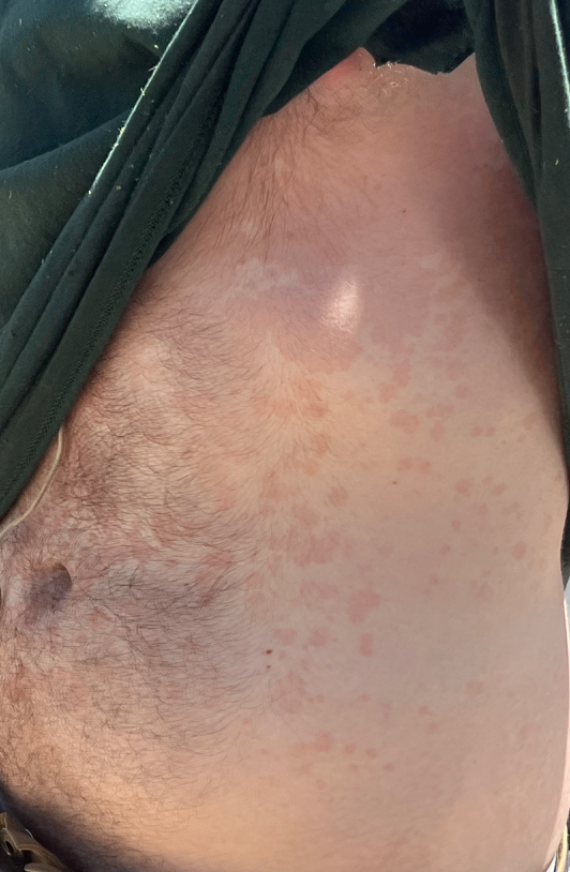differential = most consistent with Tinea Versicolor.